The contributor is 18–29, female; no constitutional symptoms were reported; this is a close-up image; texture is reported as rough or flaky; present for less than one week; symptoms reported: enlargement and bothersome appearance; located on the head or neck:
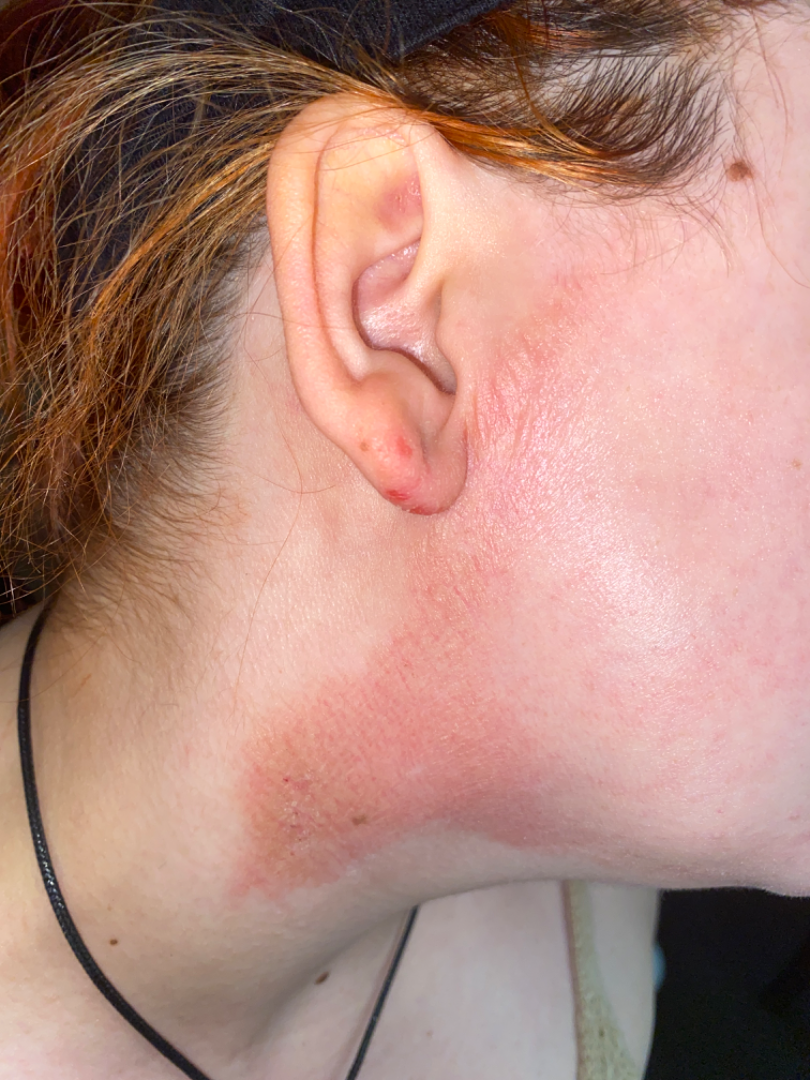Assessment:
The reviewing dermatologist's impression was: Allergic Contact Dermatitis and Irritant Contact Dermatitis were considered with similar weight.